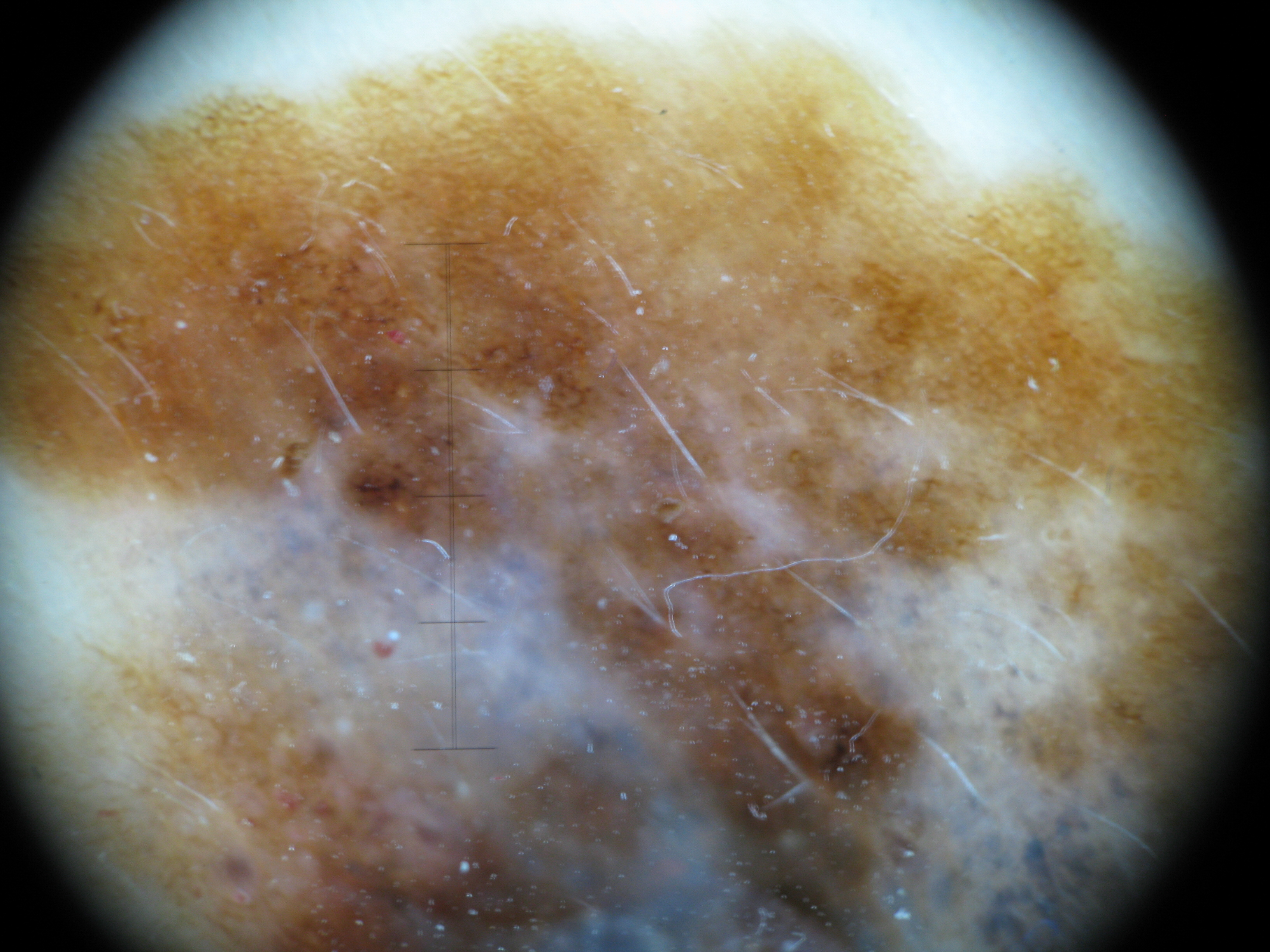A dermatoscopic image of a skin lesion. Biopsy-confirmed as a melanoma.